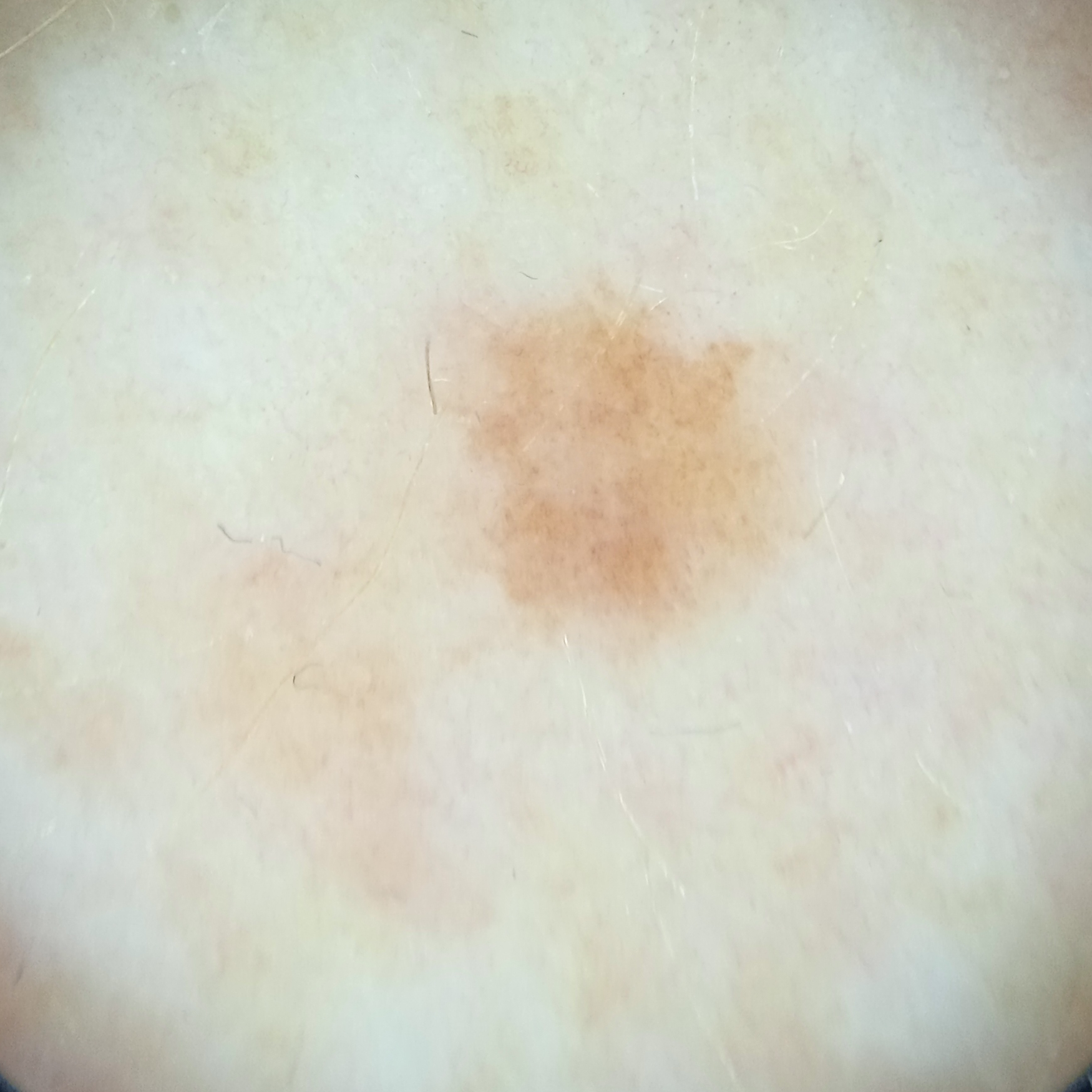{
  "mole_burden": "a moderate number of melanocytic nevi",
  "referral": "research study (no referral diagnosis)",
  "sun_reaction": "skin reddens with sun exposure",
  "risk_factors": {
    "negative": [
      "no personal history of skin cancer",
      "no prior organ transplant"
    ]
  },
  "lesion_size": {
    "diameter_mm": 4.1
  },
  "diagnosis": {
    "name": "melanocytic nevus",
    "malignancy": "benign"
  }
}